A clinical close-up photograph of a skin lesion · history notes pesticide exposure and prior skin cancer (patient or family).
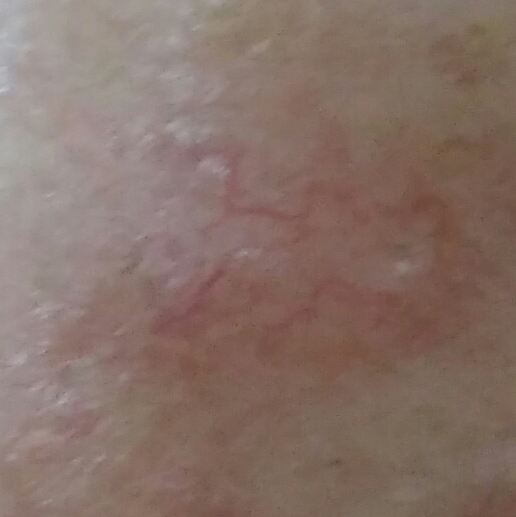Case summary:
The lesion was found on the nose. The lesion is roughly 5 by 3 mm. The patient reports that the lesion is elevated, has grown, and itches, but has not bled and does not hurt.
Pathology:
Biopsy-confirmed as a malignancy — a basal cell carcinoma.